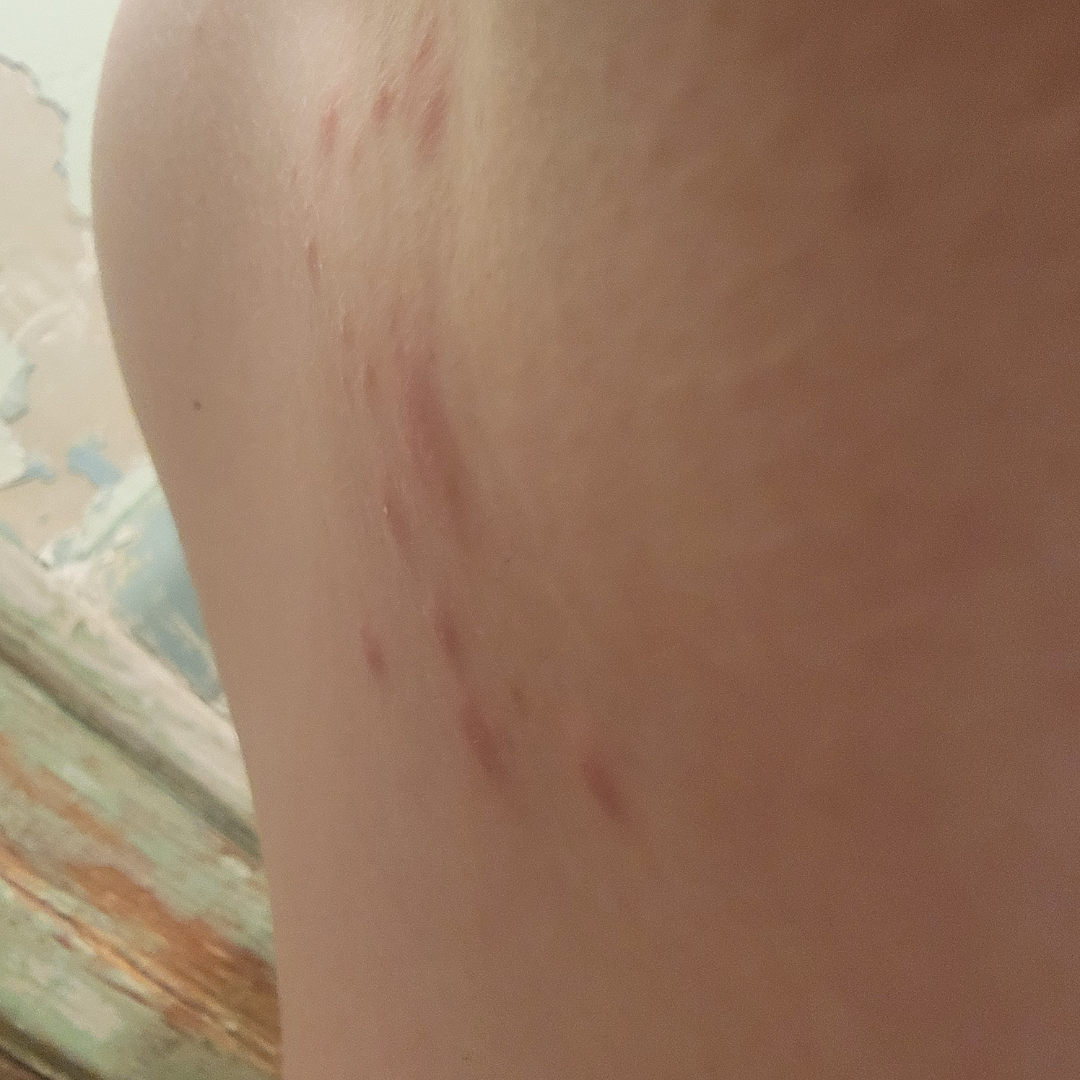The case was indeterminate on photographic review.
Female contributor, age 18–29.
The lesion is associated with enlargement and bothersome appearance.
Located on the head or neck and front of the torso.
The patient considered this acne.
The patient indicates the condition has been present for less than one week.
This image was taken at an angle.
Skin tone: Fitzpatrick skin type II.